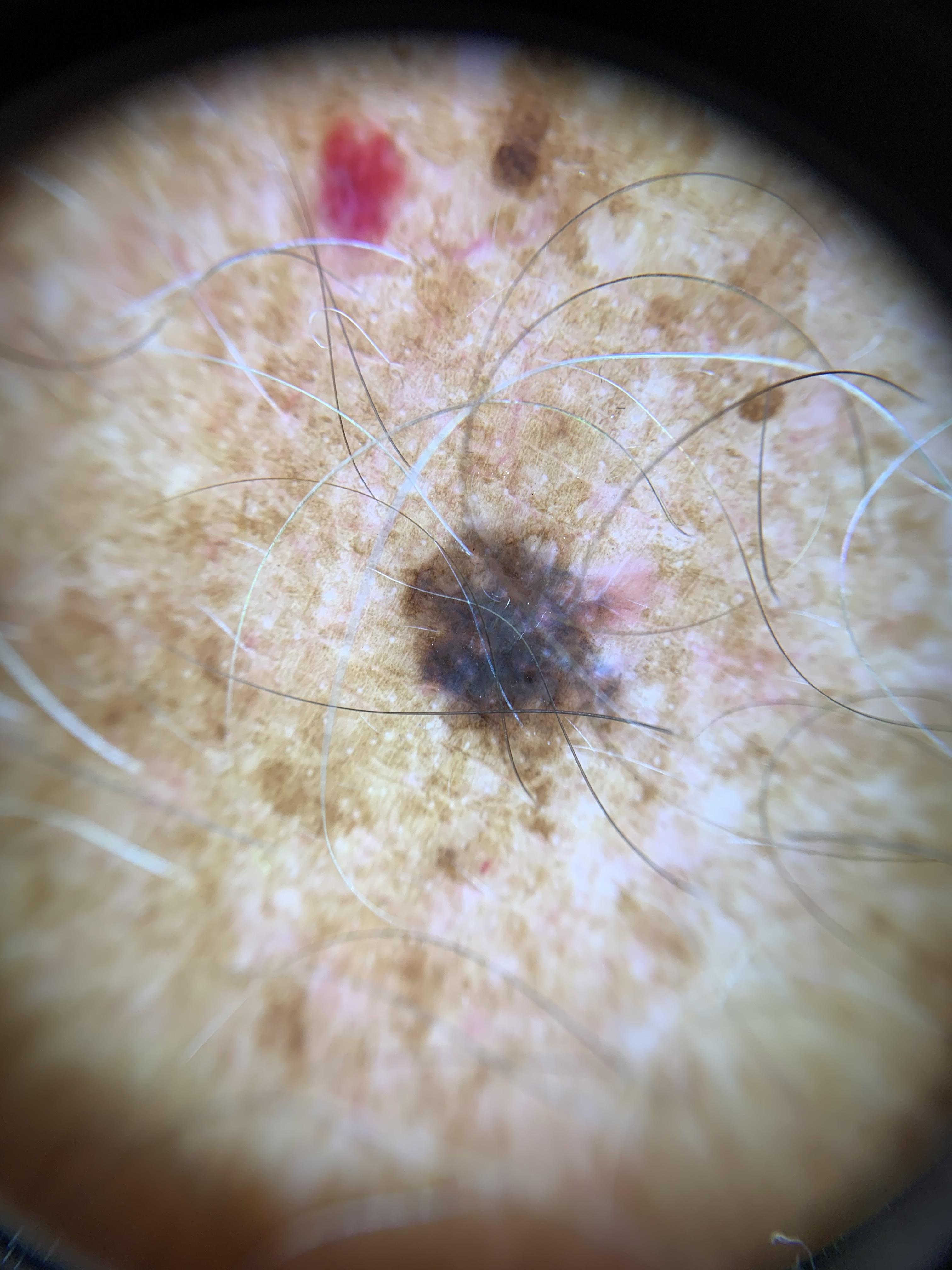Conclusion: The biopsy diagnosis was a melanoma.